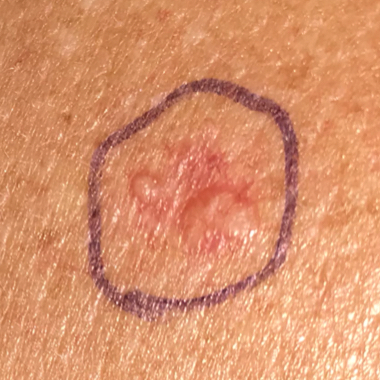FST I. A female patient 43 years of age. The chart notes prior skin cancer (patient or family), no tobacco use, and no pesticide exposure. A clinical photograph showing a skin lesion. The lesion involves the back. The lesion measures approximately 11 × 8 mm. Biopsy-confirmed as a malignant lesion — a basal cell carcinoma.